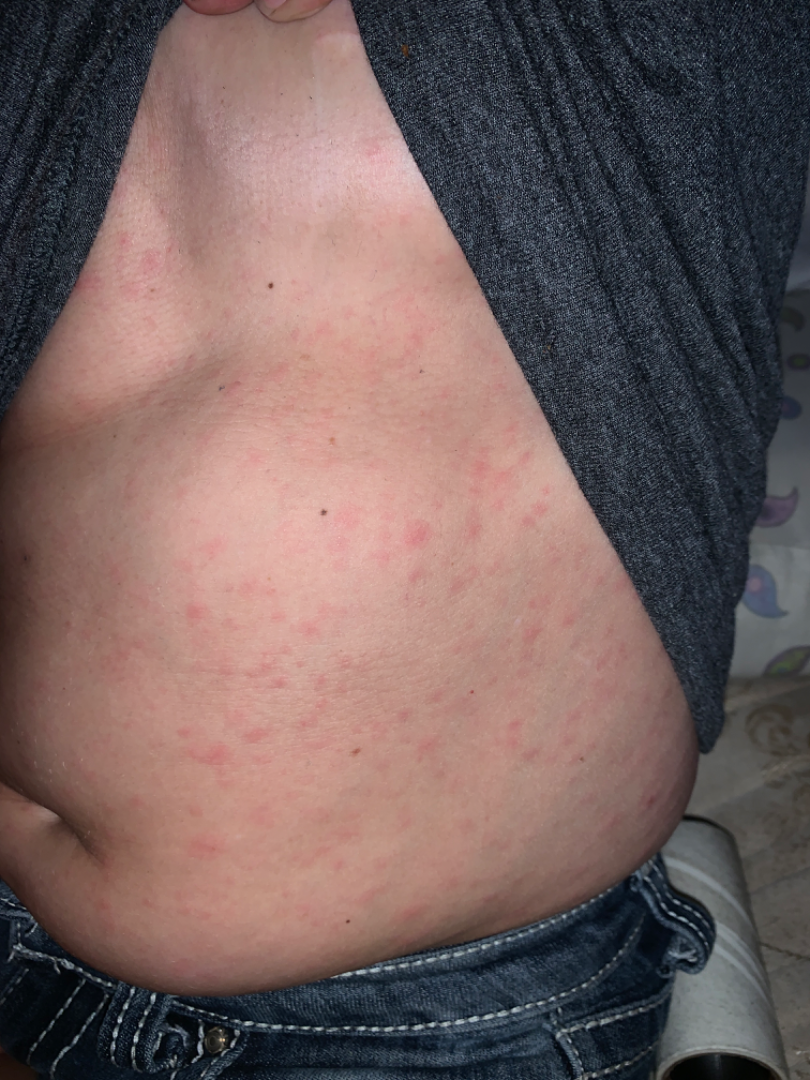The condition could not be reliably identified from the image.